A female patient 26 years of age · a clinical close-up of a skin lesion · collected as part of a research study, without a referral diagnosis — 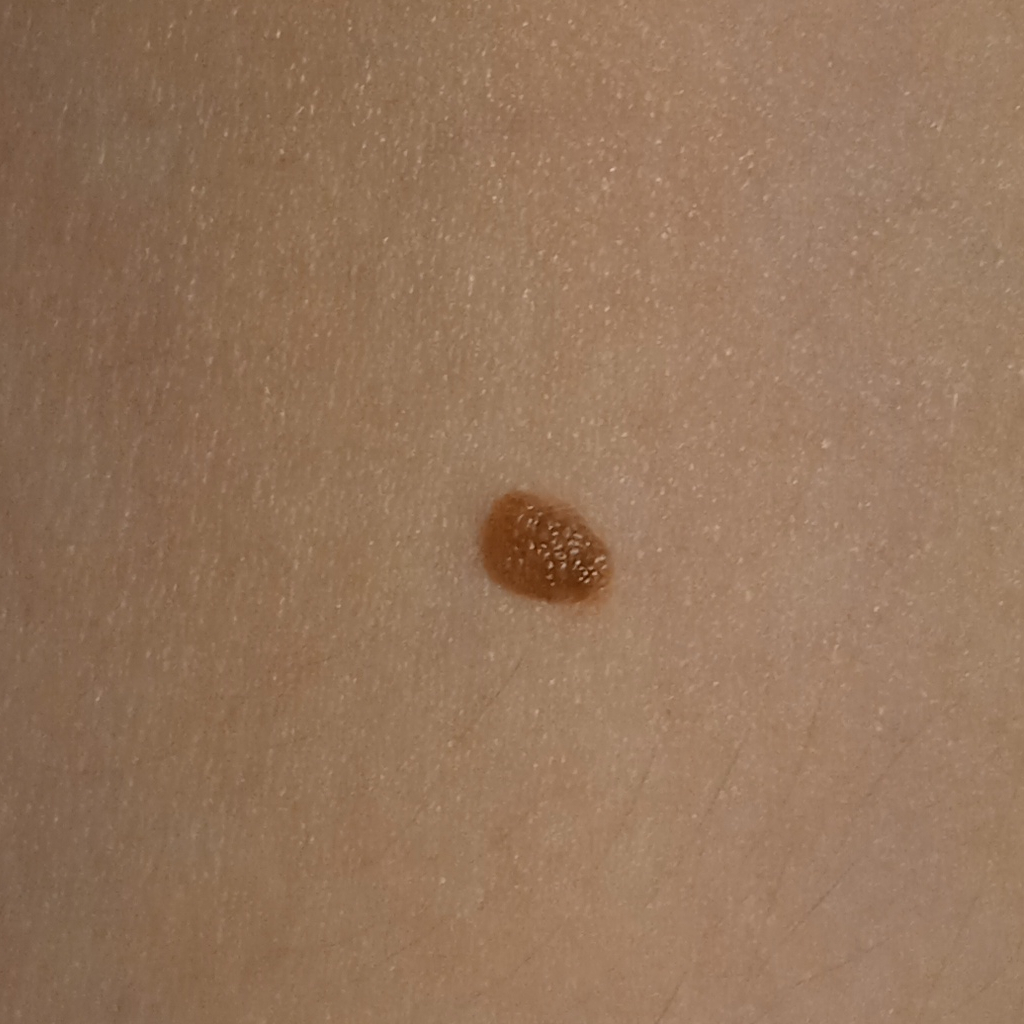Case:
* lesion size · 5.5 mm
* assessment · melanocytic nevus (dermatologist consensus)